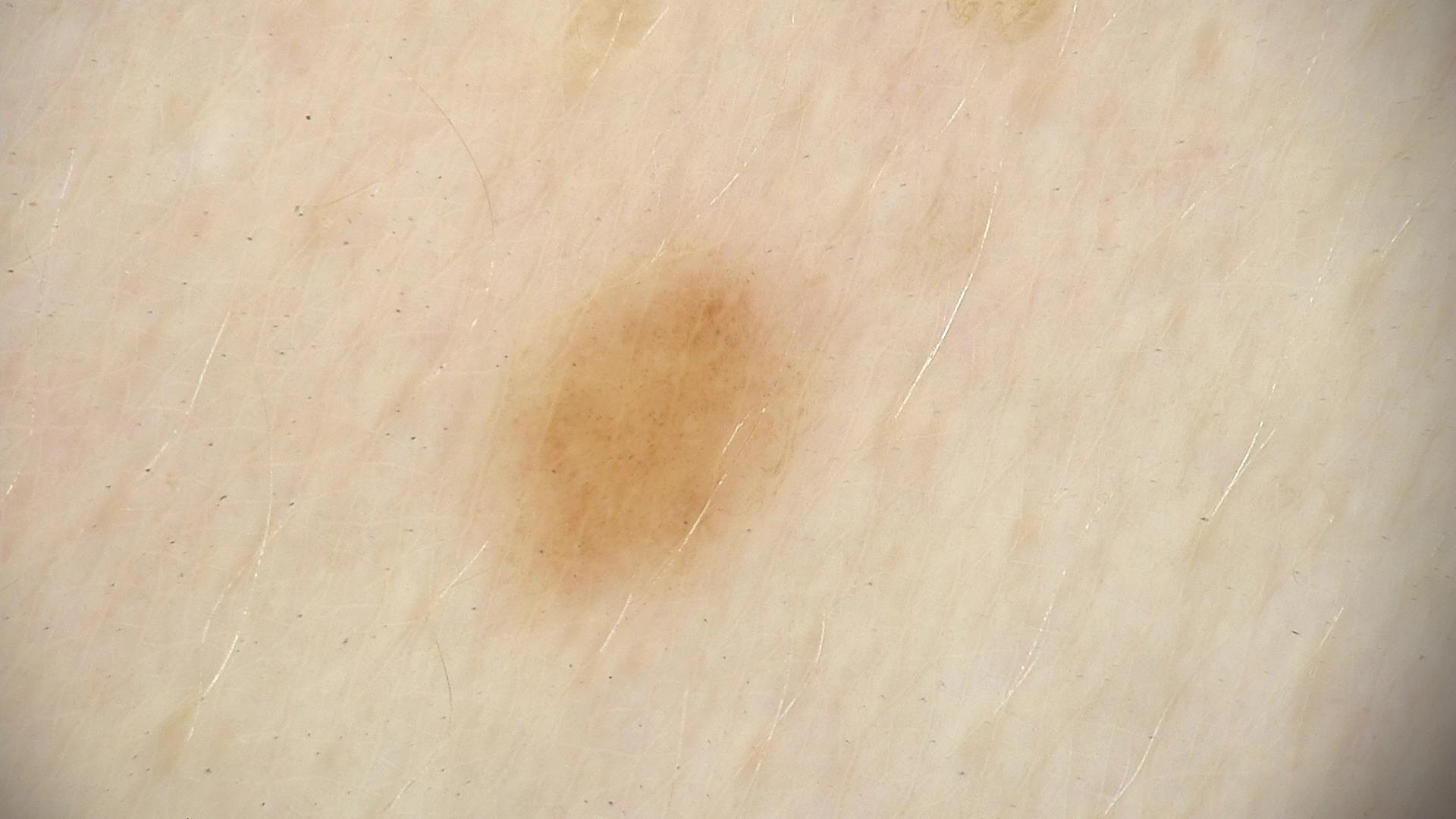Q: What is this lesion?
A: dysplastic junctional nevus (expert consensus)